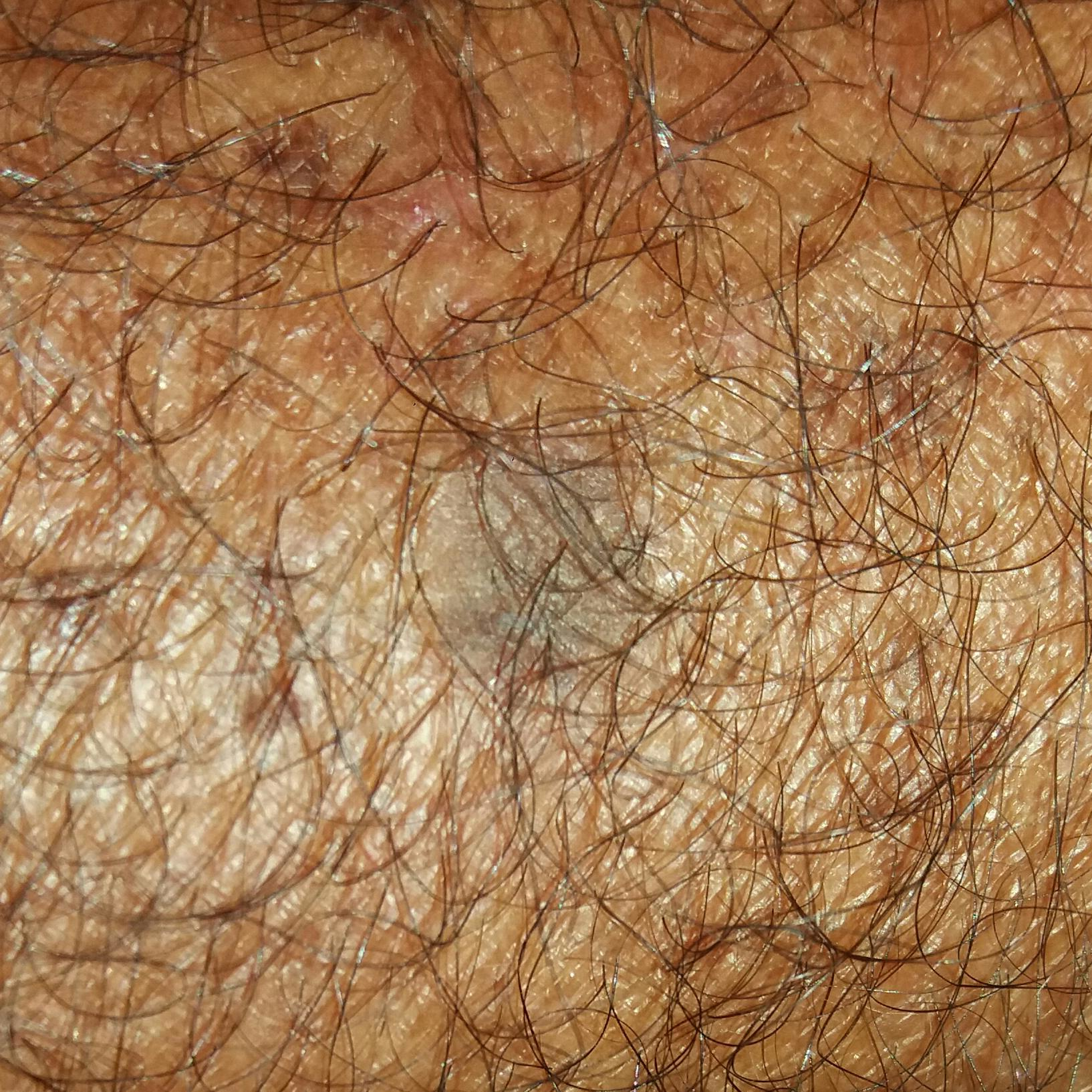Impression:
Clinically diagnosed as a seborrheic keratosis.